Close-up view. The patient reports itching and bothersome appearance. Human graders estimated Monk Skin Tone 1–2. The affected area is the arm. Present for one to four weeks. Texture is reported as flat — 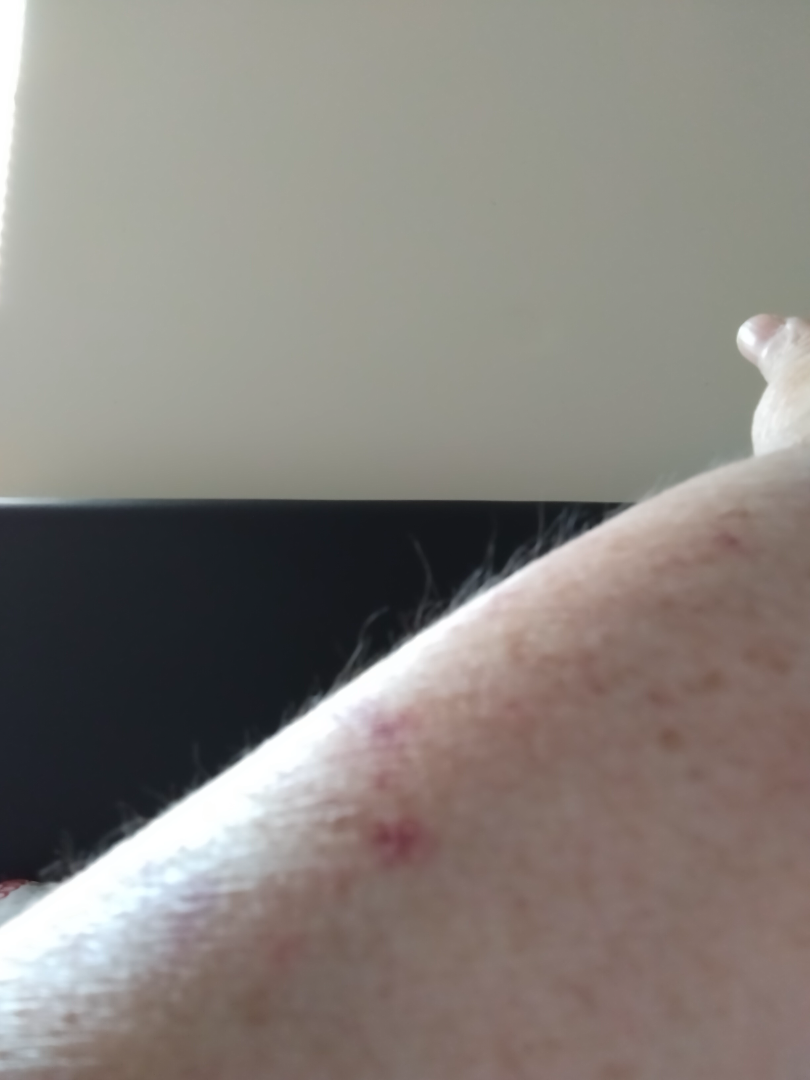assessment = indeterminate.